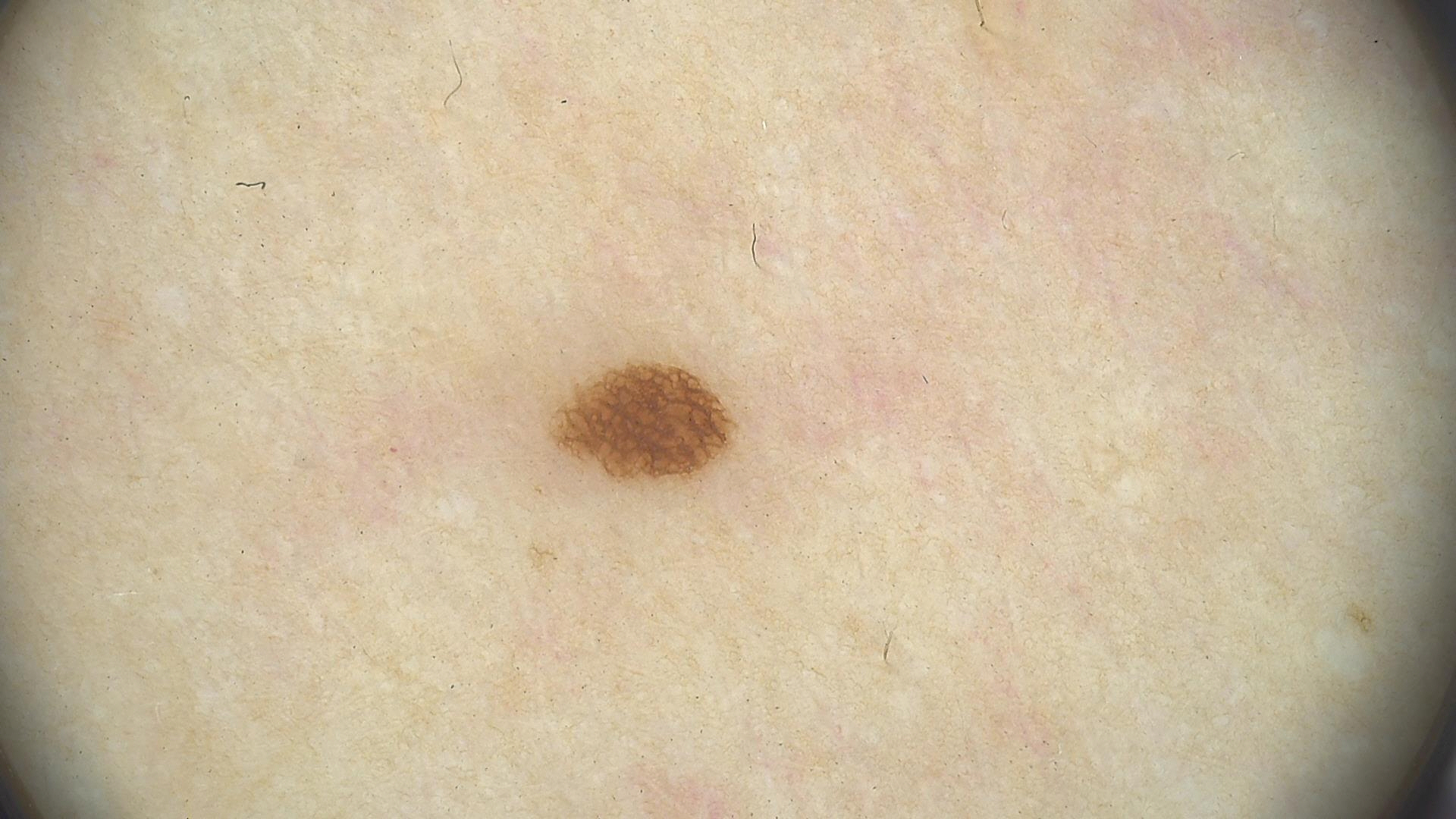Diagnosed as a junctional nevus.